A dermatoscopic image of a skin lesion · the patient reports no personal history of cancer: 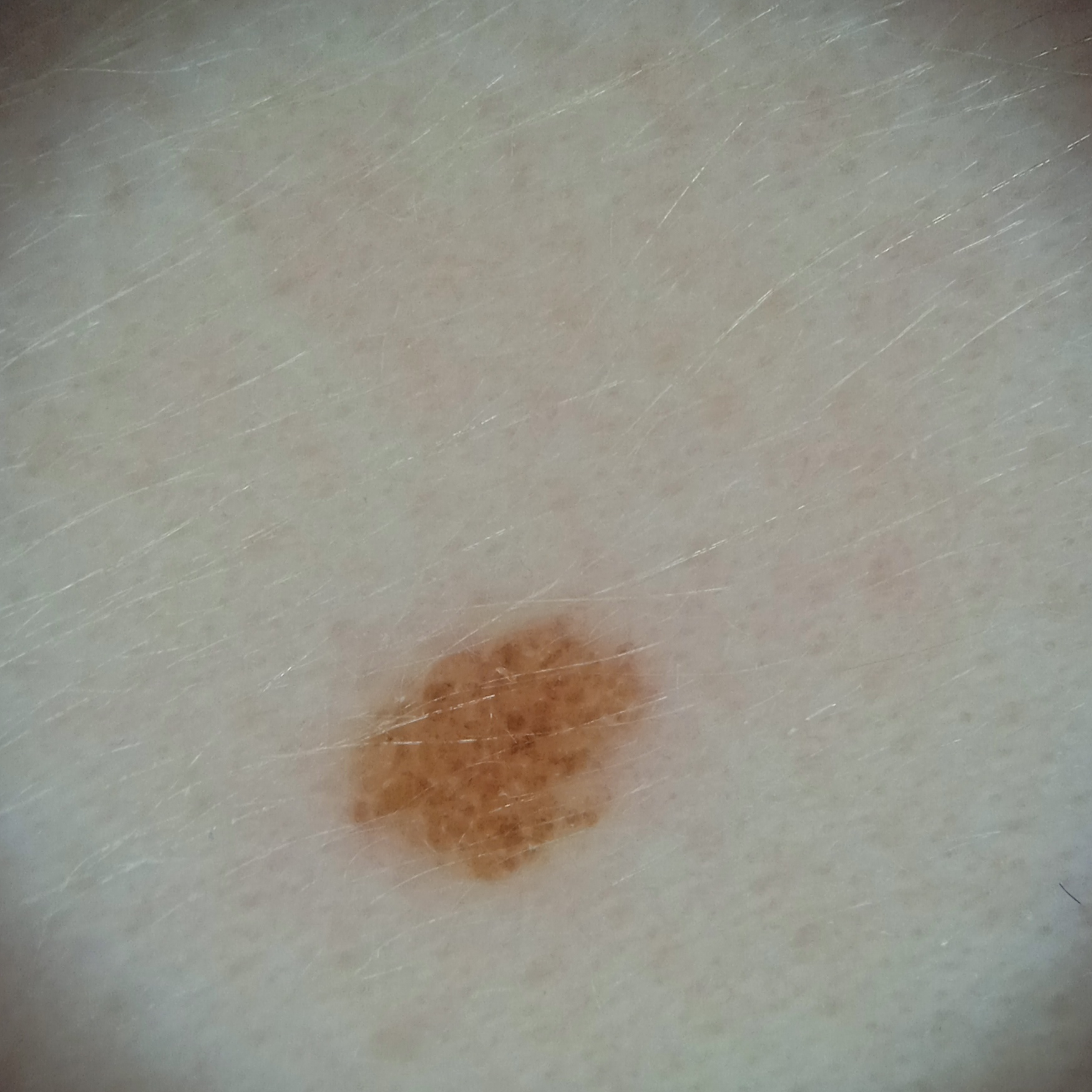The lesion involves the face. On independent review by four dermatologists, the agreed diagnosis was a melanocytic nevus; all four reviewers agreed.